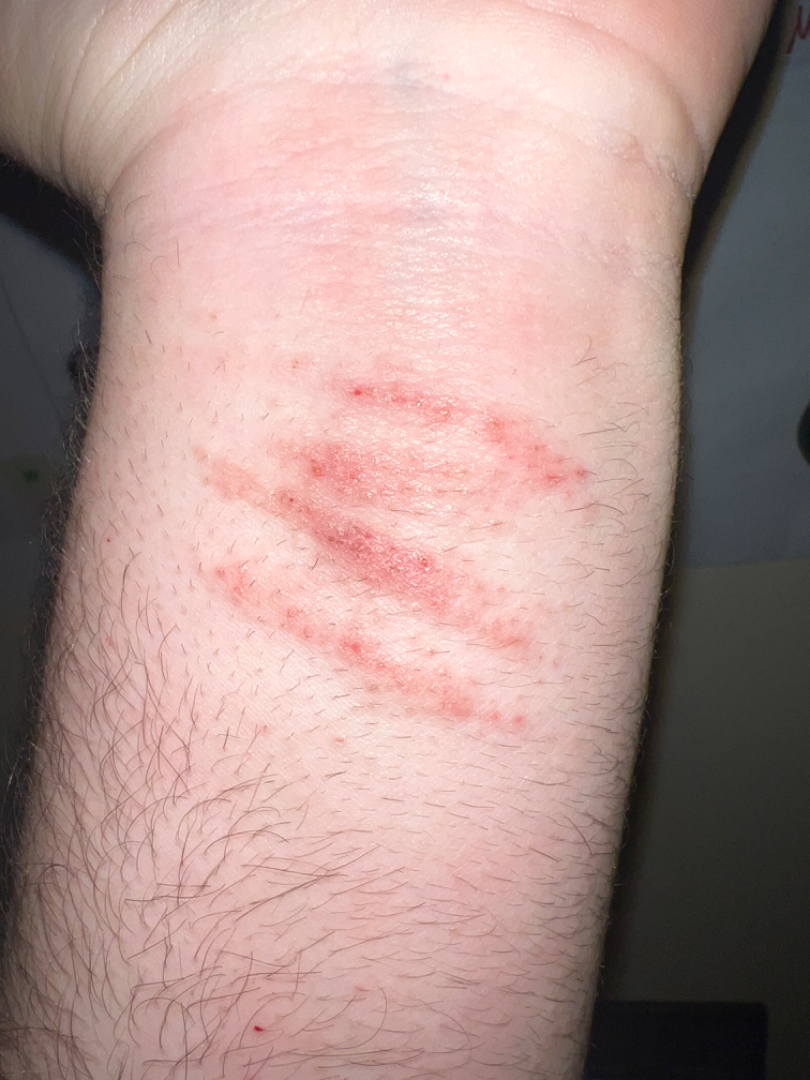| key | value |
|---|---|
| patient | male, age 18–29 |
| lesion texture | raised or bumpy |
| patient-reported symptoms | itching and enlargement |
| location | arm |
| onset | one to four weeks |
| view | close-up |
| patient's own categorization | a rash |
| dermatologist impression | the favored diagnosis is Allergic Contact Dermatitis; also raised was Contact dermatitis; less probable is Irritant Contact Dermatitis; a remote consideration is Abrasion of wrist; less likely is Animal bite - wound |